A dermoscopic close-up of a skin lesion.
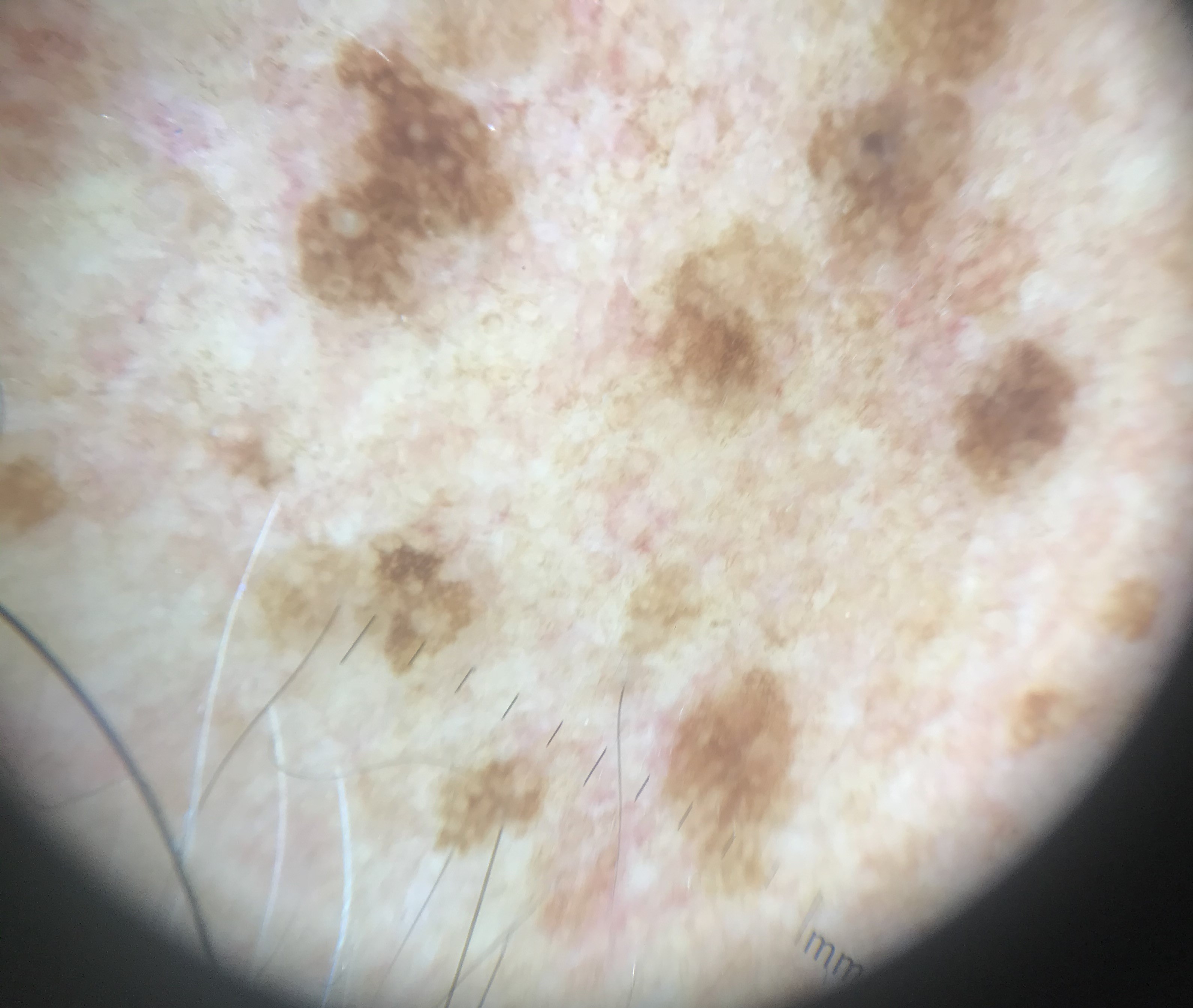The architecture is that of a keratinocytic lesion.
Classified as a seborrheic keratosis.